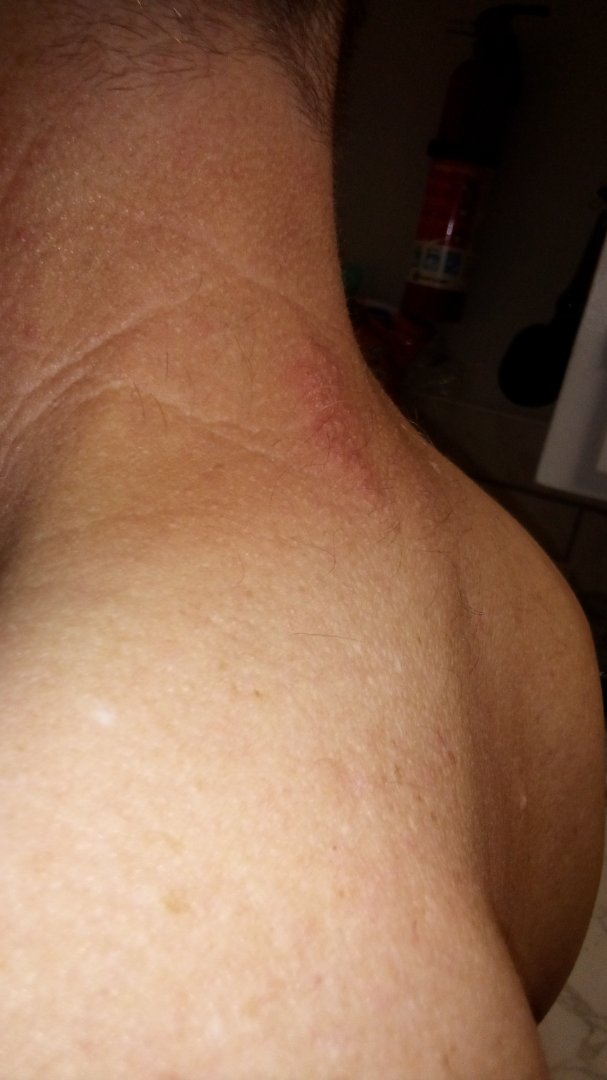The condition could not be reliably identified from the image.